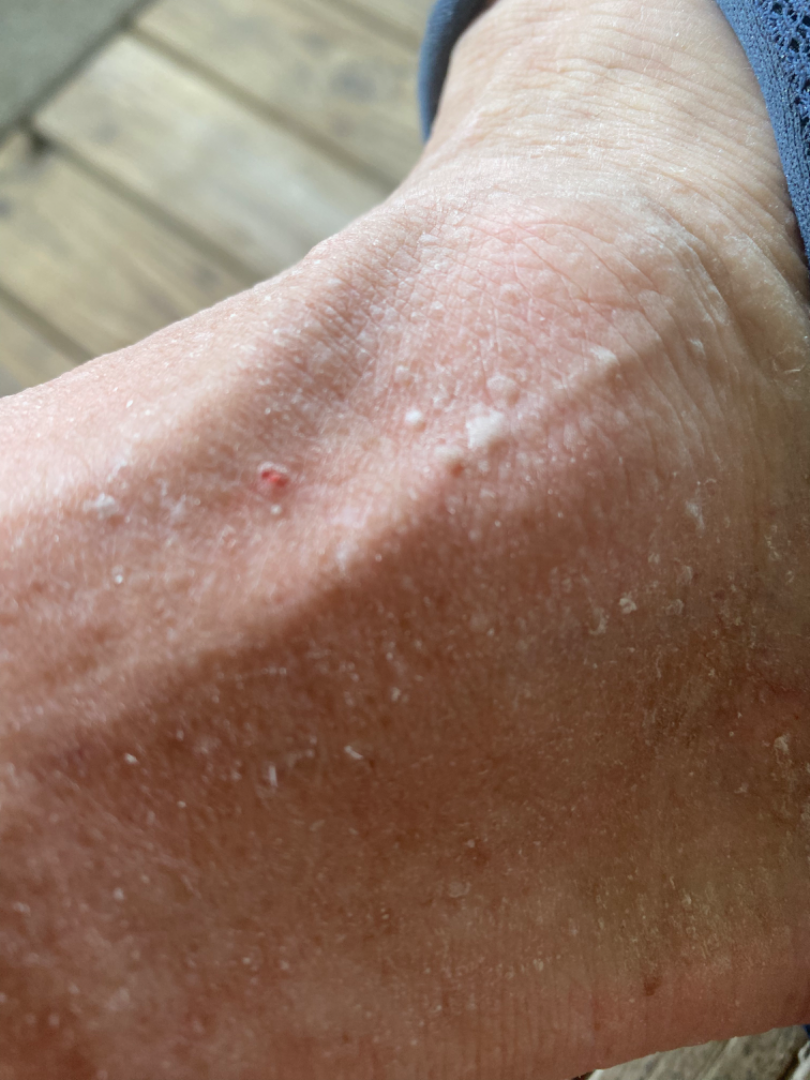Findings:
• texture — raised or bumpy
• present for — one to four weeks
• framing — close-up
• site — leg